A dermoscopic photograph of a skin lesion.
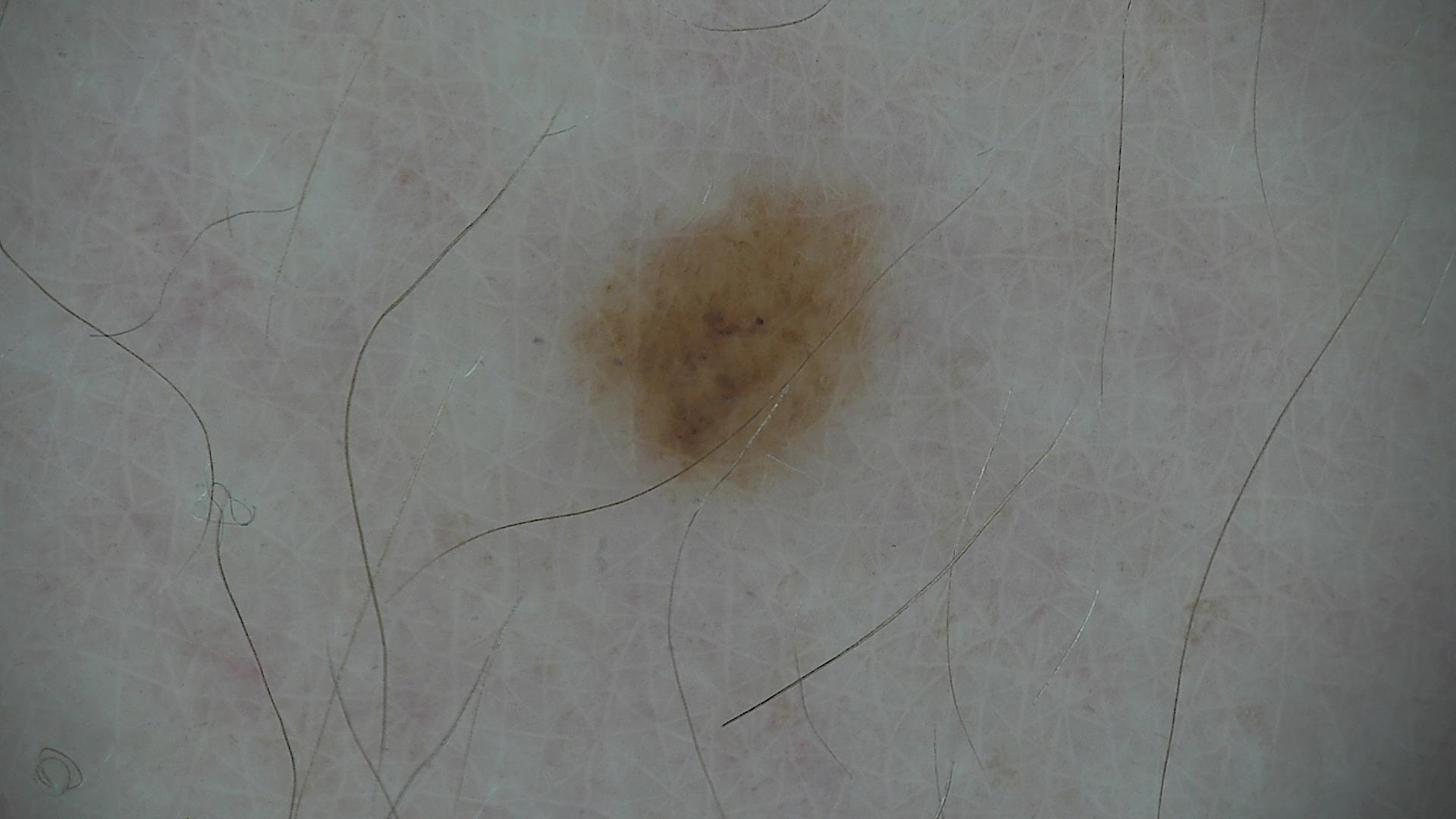Diagnosed as a banal lesion — a junctional nevus.